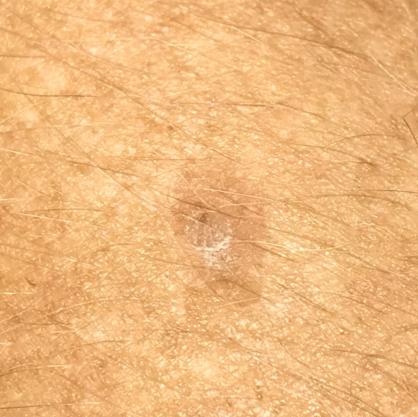Clinical context:
A patient aged 72. The lesion involves a forearm. The patient reports that the lesion has grown, is elevated, and itches, but does not hurt and has not changed.
Impression:
The consensus clinical diagnosis was a seborrheic keratosis.